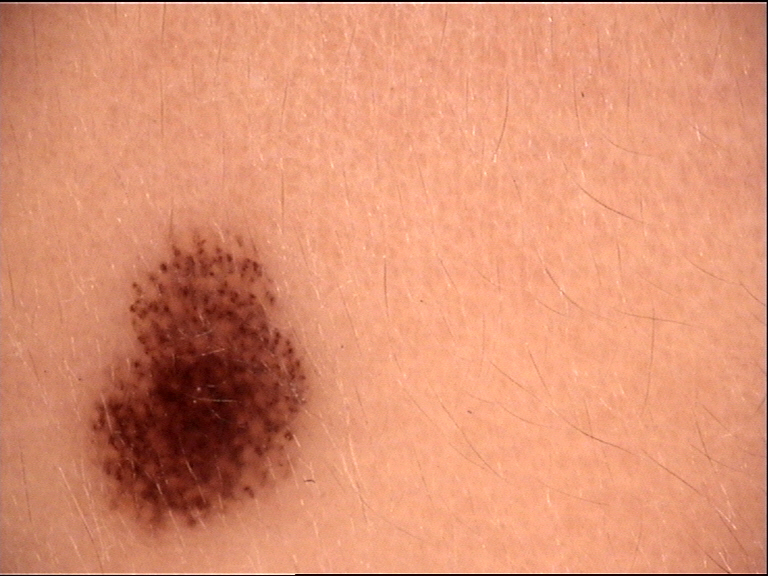Labeled as a dysplastic junctional nevus.